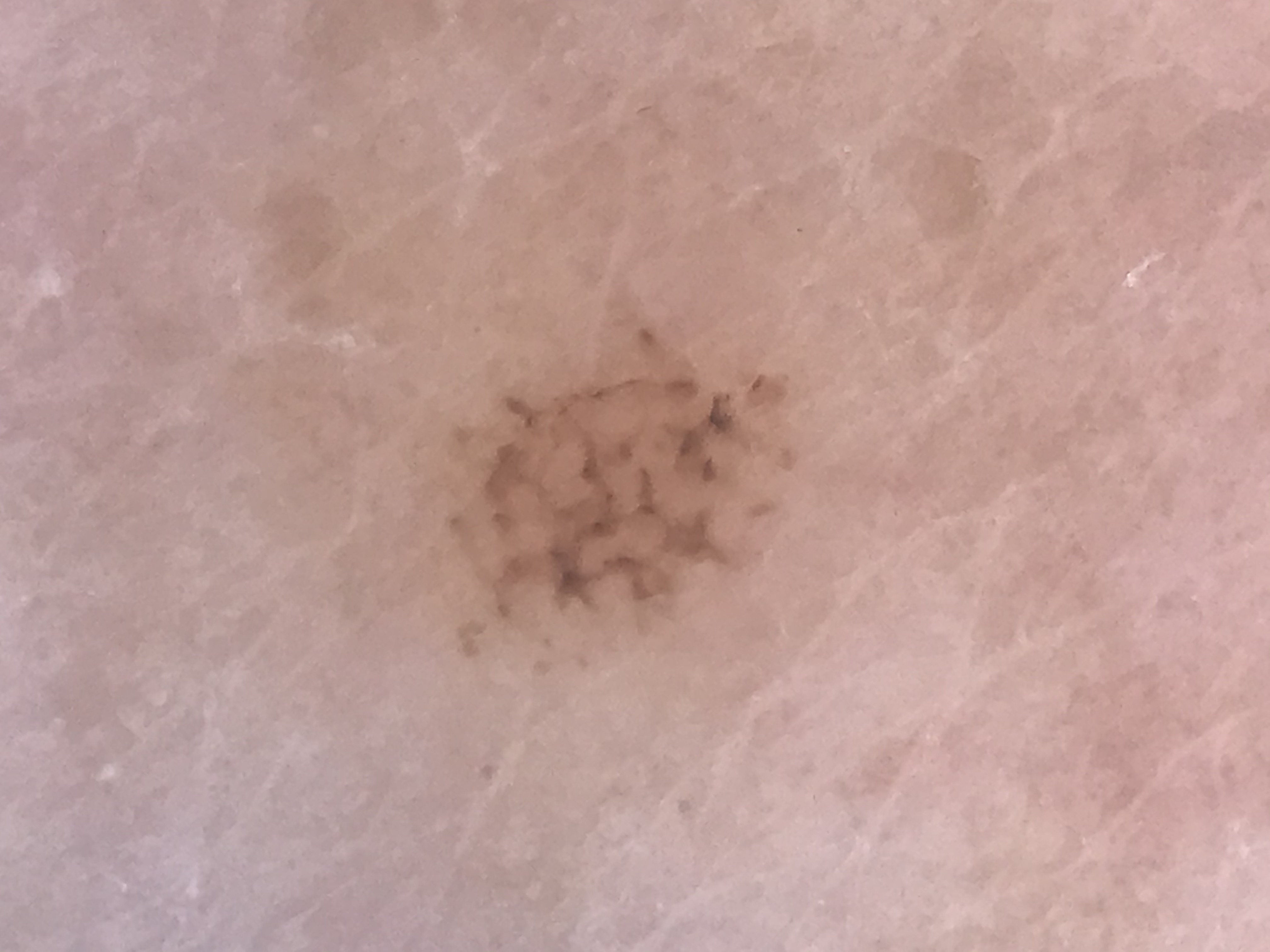Conclusion: The diagnostic label was a benign lesion — an acral dysplastic junctional nevus.